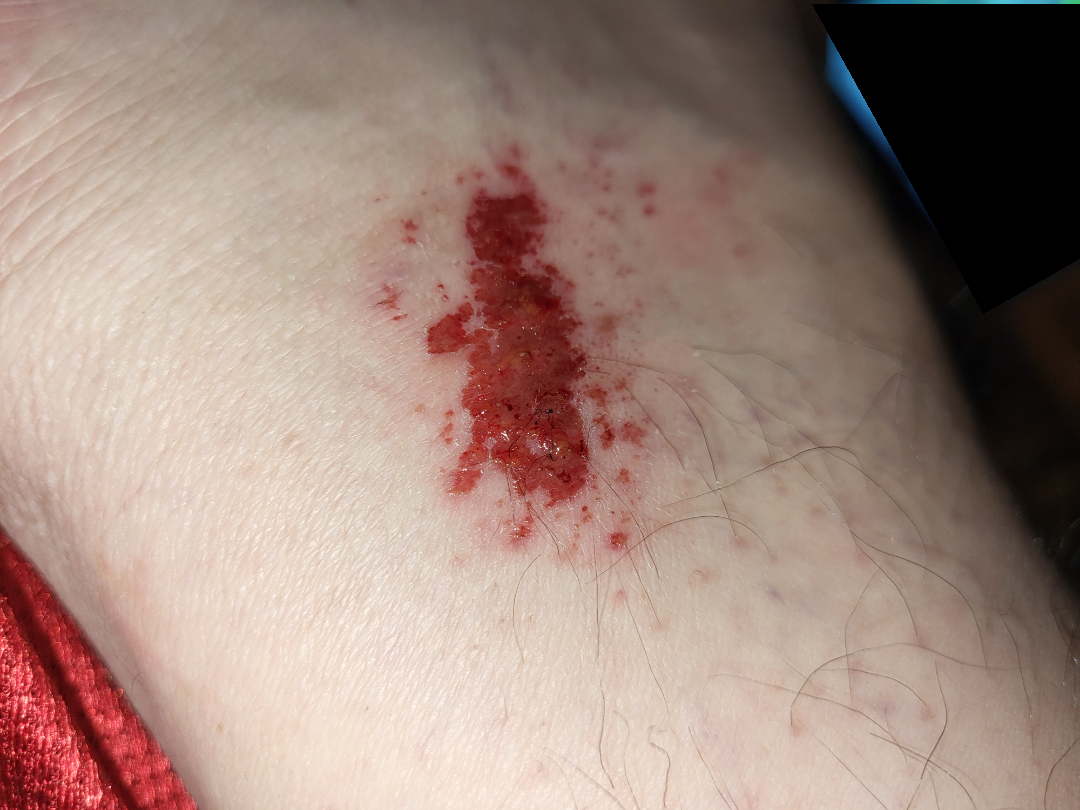Reviewed remotely by one dermatologist: most consistent with Superficial wound of body region; also on the differential is superficial hemorrhage; also raised was Blister.